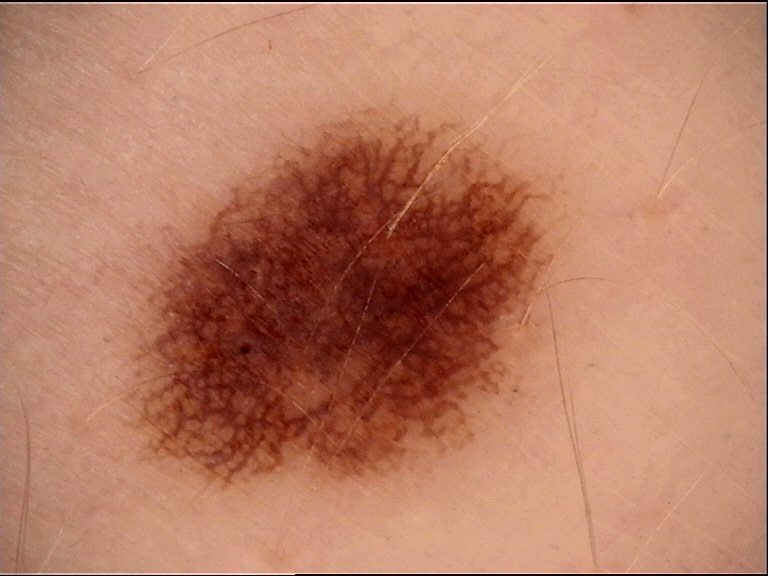Conclusion: Consistent with a benign lesion — a dysplastic junctional nevus.